A dermoscopic close-up of a skin lesion:
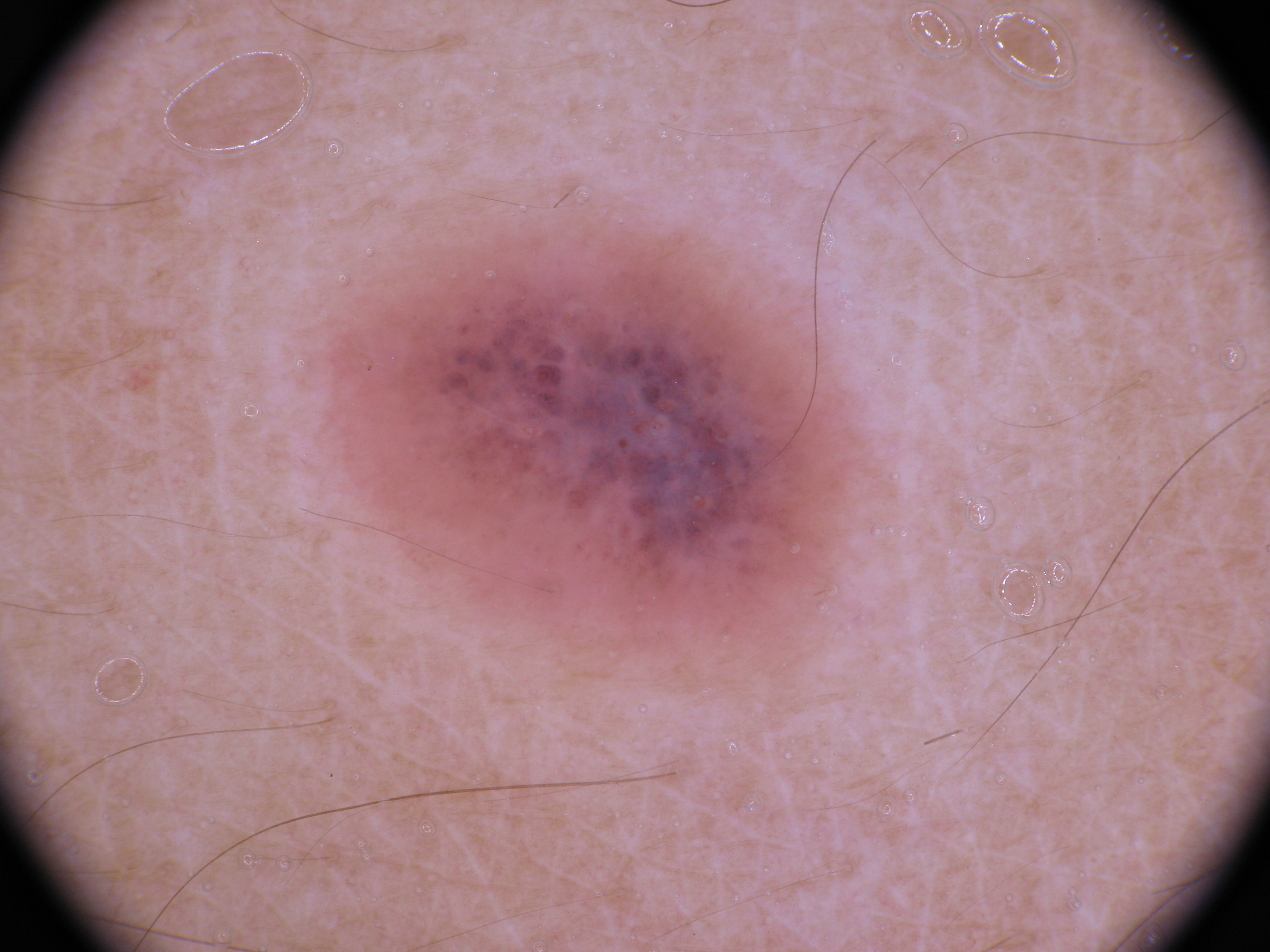On dermoscopy, the lesion shows no pigment network, milia-like cysts, streaks, globules, or negative network. The lesion takes up a moderate portion of the field. As (left, top, right, bottom), the lesion is located at 305/211/872/699. The clinical diagnosis was a melanocytic nevus, a benign skin lesion.